A clinical photograph showing a skin lesion · history notes prior malignancy (patient or family), pesticide exposure, and prior skin cancer (patient or family) · a male subject 58 years old · the patient is Fitzpatrick phototype I.
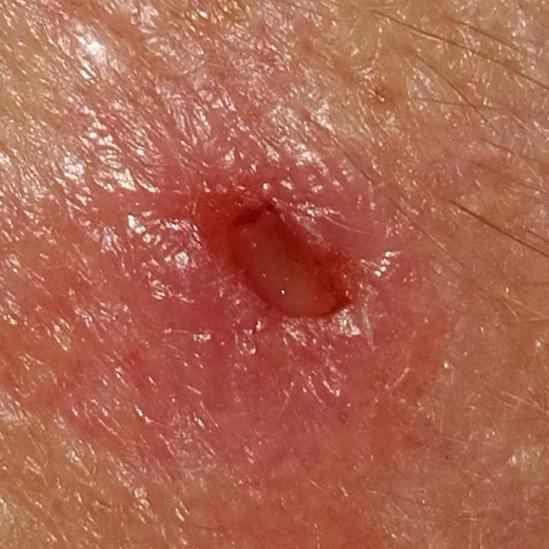The lesion involves the face. Measuring about 10 × 7 mm. The patient reports that the lesion has bled, has grown, is elevated, itches, has changed, and hurts. Histopathology confirmed a basal cell carcinoma.